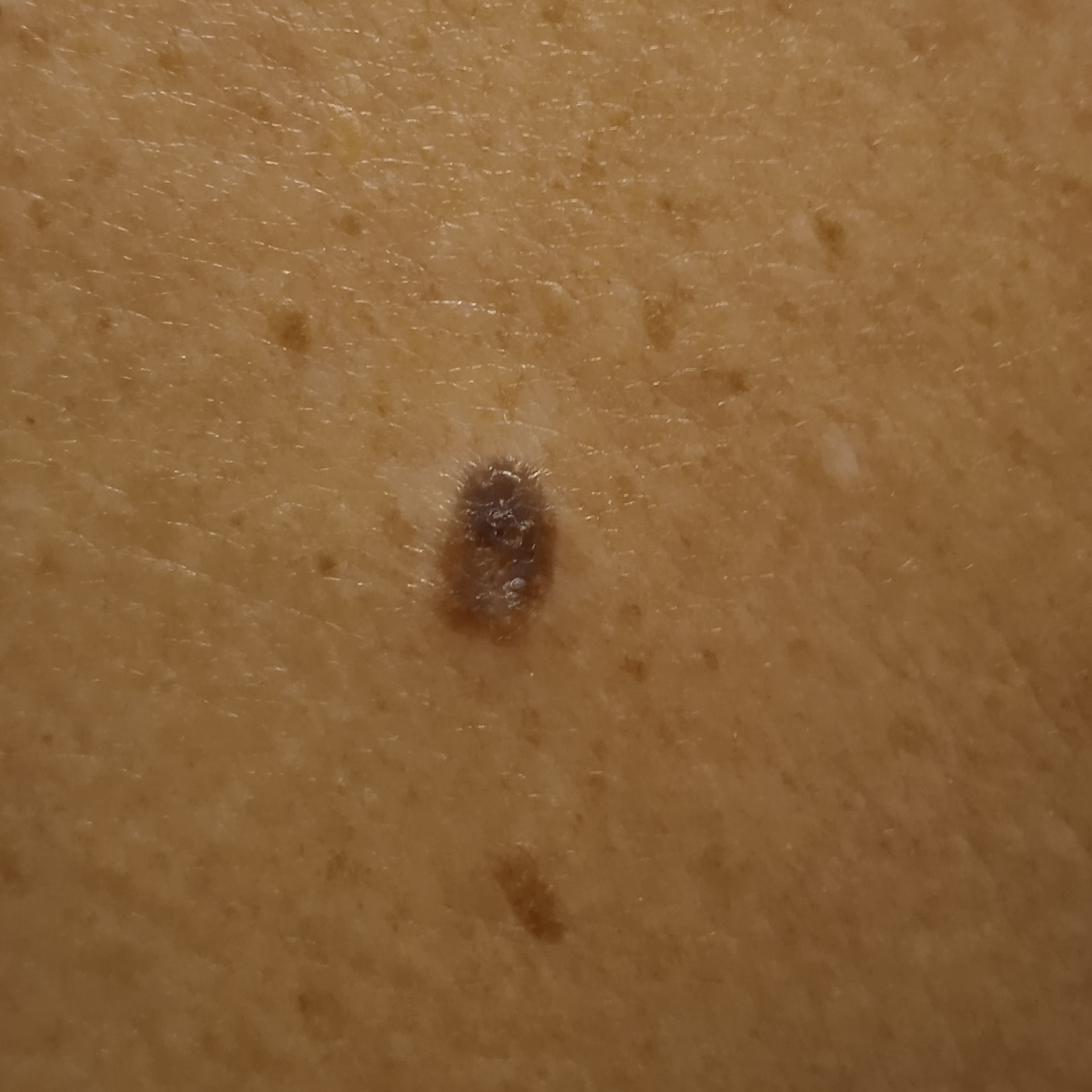| feature | finding |
|---|---|
| nevus count | a moderate number of melanocytic nevi |
| image | clinical photograph |
| patient | male, 72 years of age |
| site | the back |
| size | 8.1 mm |
| assessment | seborrheic keratosis (dermatologist consensus) |